Texture is reported as rough or flaky; present for one to four weeks; symptoms reported: bothersome appearance and itching; no constitutional symptoms were reported; a close-up photograph; Fitzpatrick phototype II; the patient considered this a rash; located on the leg, back of the torso and arm: 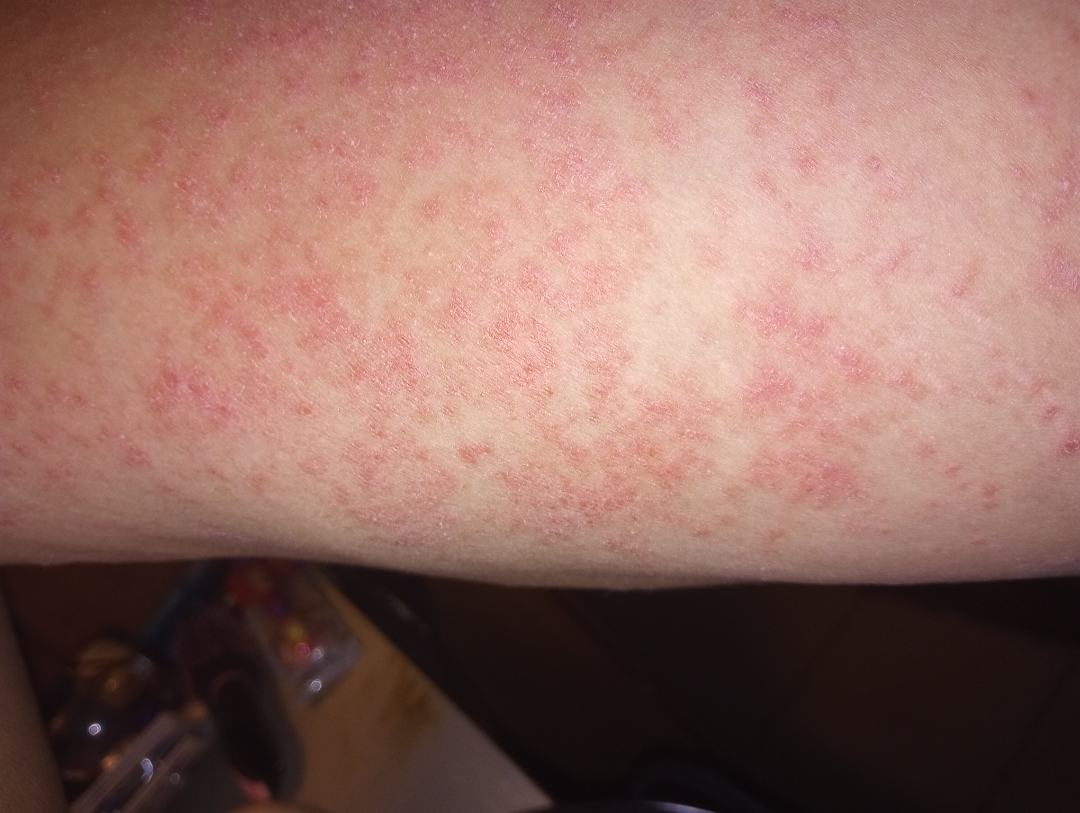Impression: Favoring Eczema; also raised was Psoriasis; lower on the differential is Drug Rash.